A female subject age 26. The patient says their skin reddens with sun exposure. Numerous moles by the patient's own estimate. On a questionnaire the patient reported a history of sunbed use, no prior organ transplant, and no personal history of cancer. Imaged for a research study, with no referral diagnosis recorded. Dermoscopy of a skin lesion — 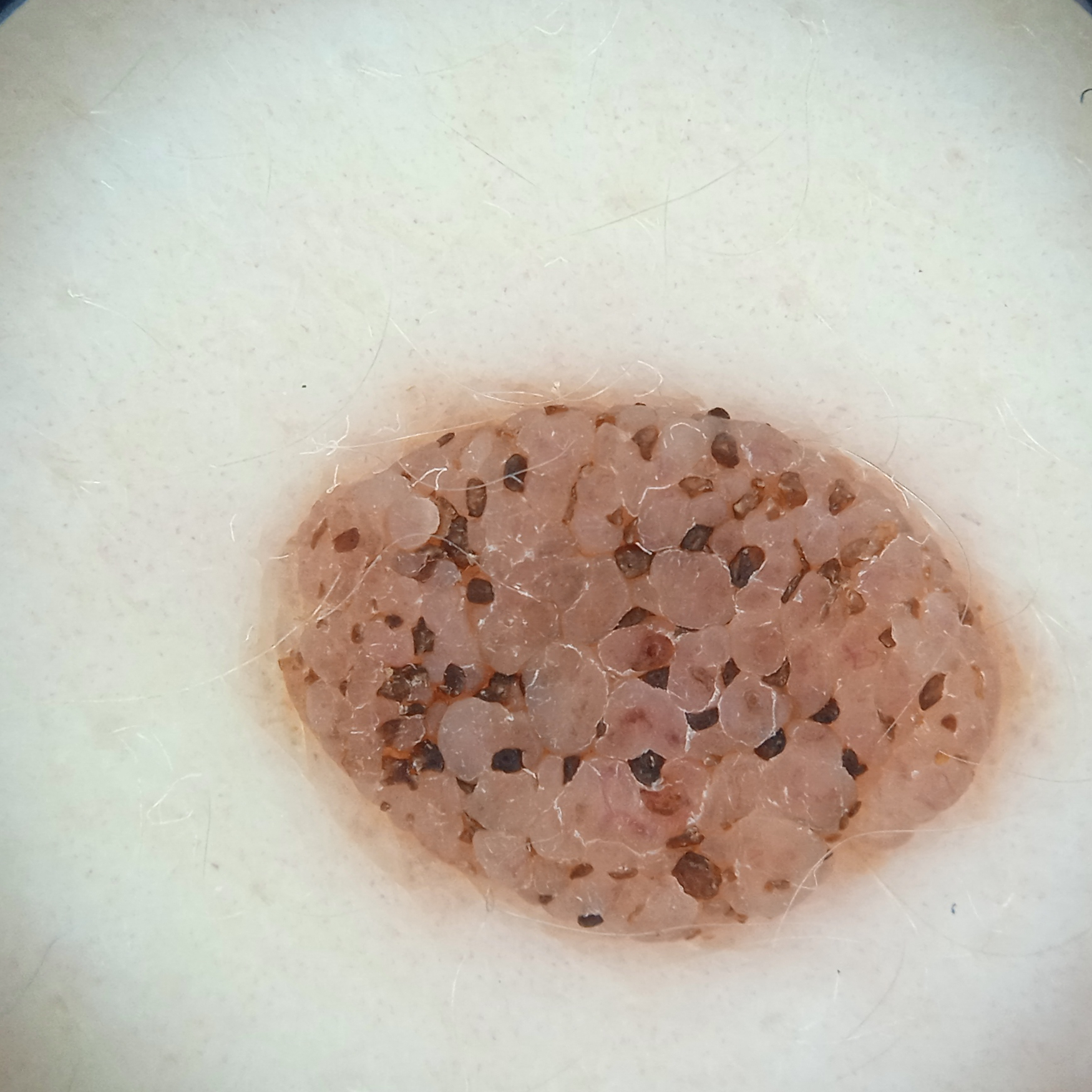Summary: Located on the back. Measuring roughly 8.4 mm. Impression: The lesion was assessed as a seborrheic keratosis.